A dermoscopic close-up of a skin lesion:
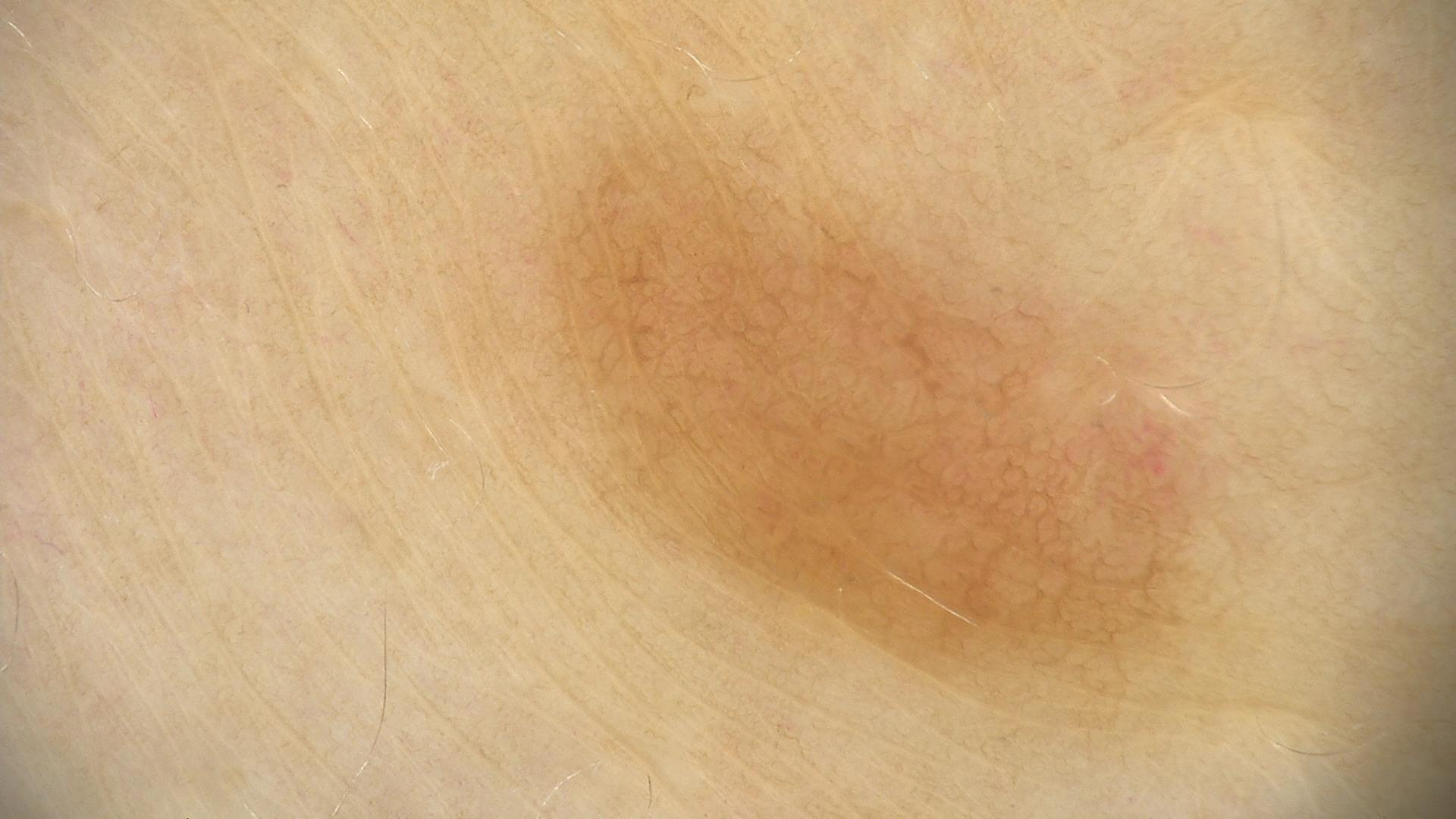<dermoscopy>
<diagnosis>
<name>dysplastic junctional nevus</name>
<code>jd</code>
<malignancy>benign</malignancy>
<super_class>melanocytic</super_class>
<confirmation>expert consensus</confirmation>
</diagnosis>
</dermoscopy>